The photo was captured at a distance; texture is reported as fluid-filled; located on the leg; no relevant lesion symptoms reported; the patient described the issue as acne; no relevant systemic symptoms; reported duration is about one day; the contributor is female.
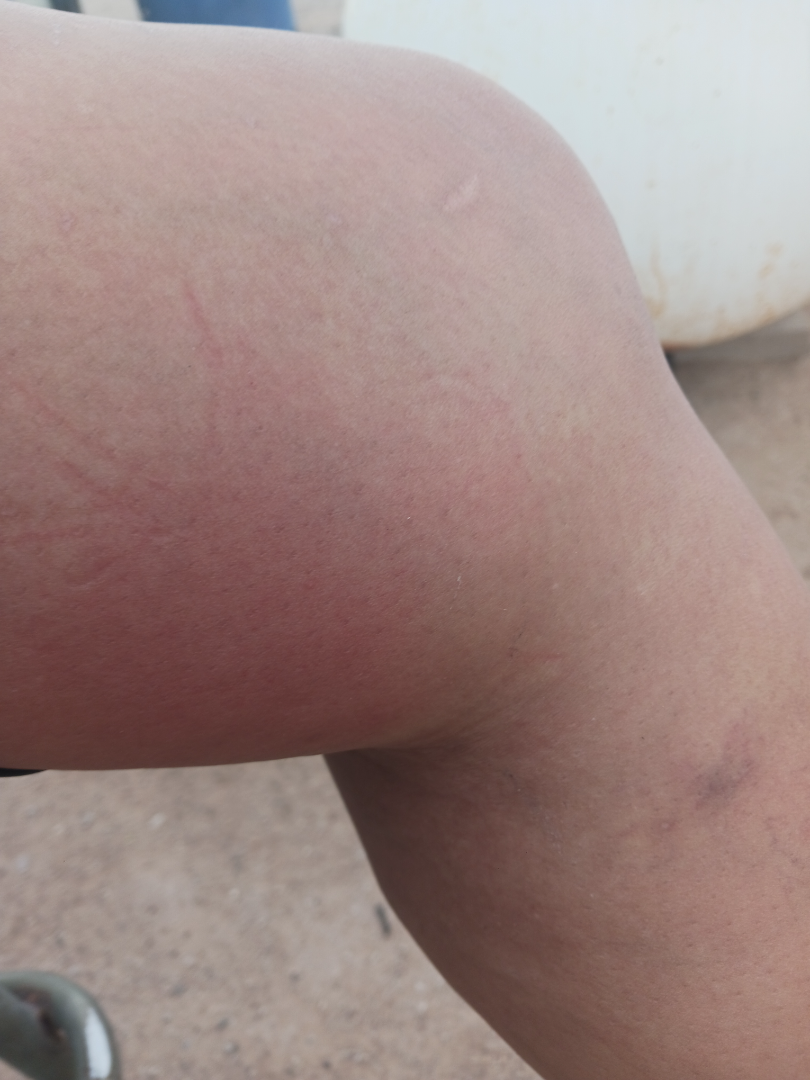  differential:
    tied_lead:
      - Cellulitis
      - Eczema
    unlikely:
      - Insect Bite
      - deep vein thrombosis